A dermoscopic photograph of a skin lesion.
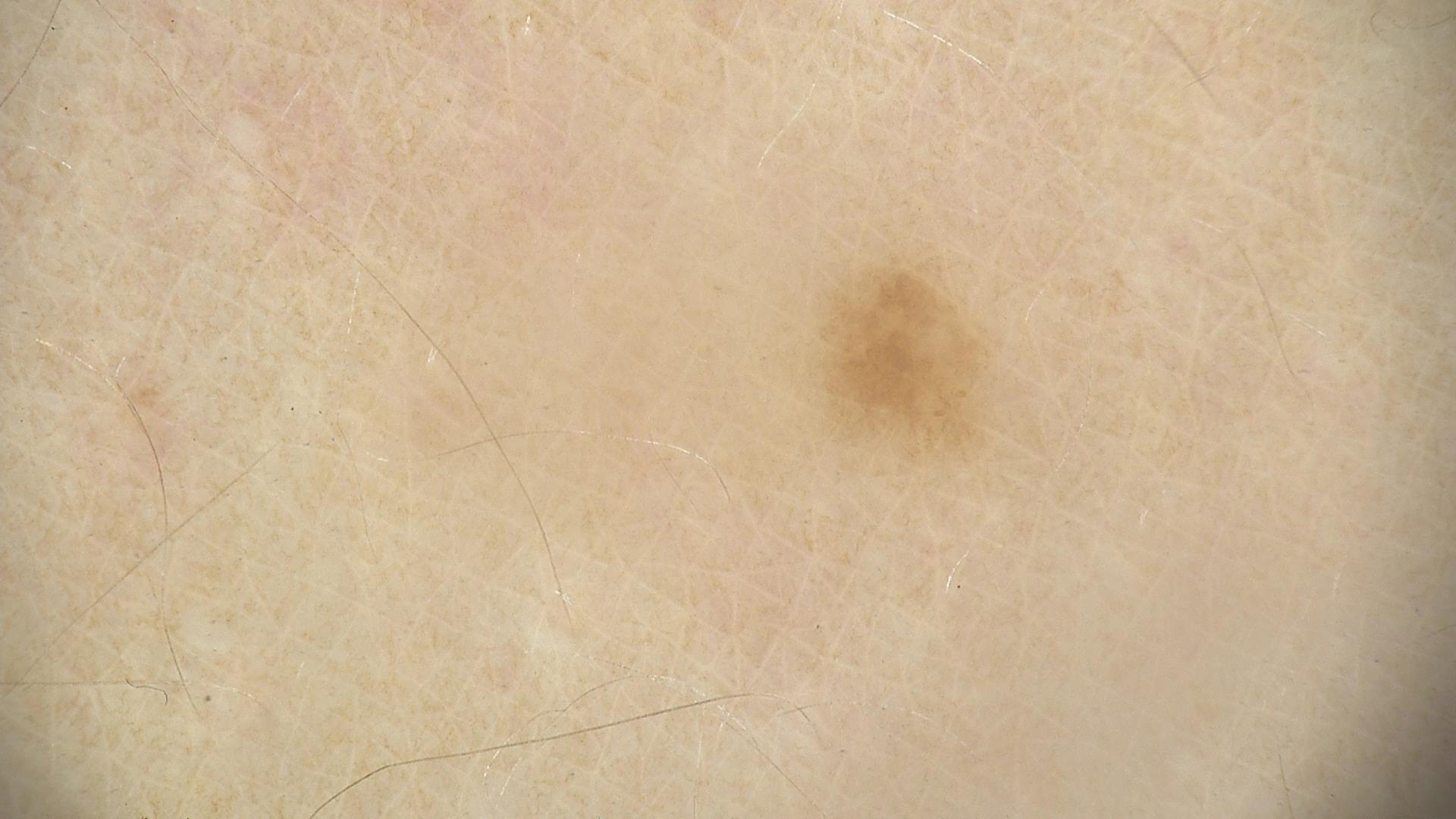<case>
<diagnosis>
<name>lentigo simplex</name>
<code>ls</code>
<malignancy>benign</malignancy>
<super_class>melanocytic</super_class>
<confirmation>expert consensus</confirmation>
</diagnosis>
</case>